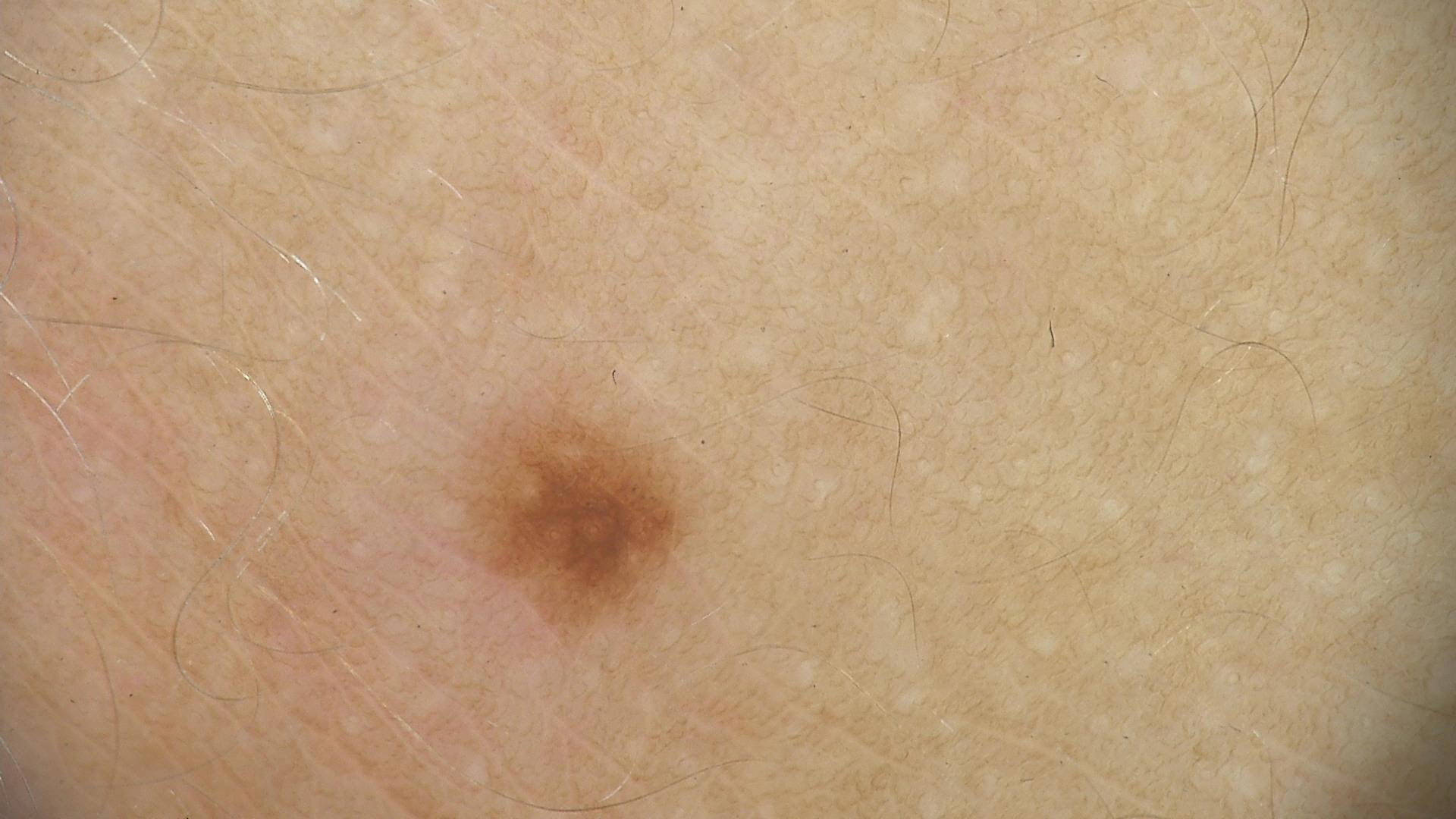Classified as a dysplastic junctional nevus.